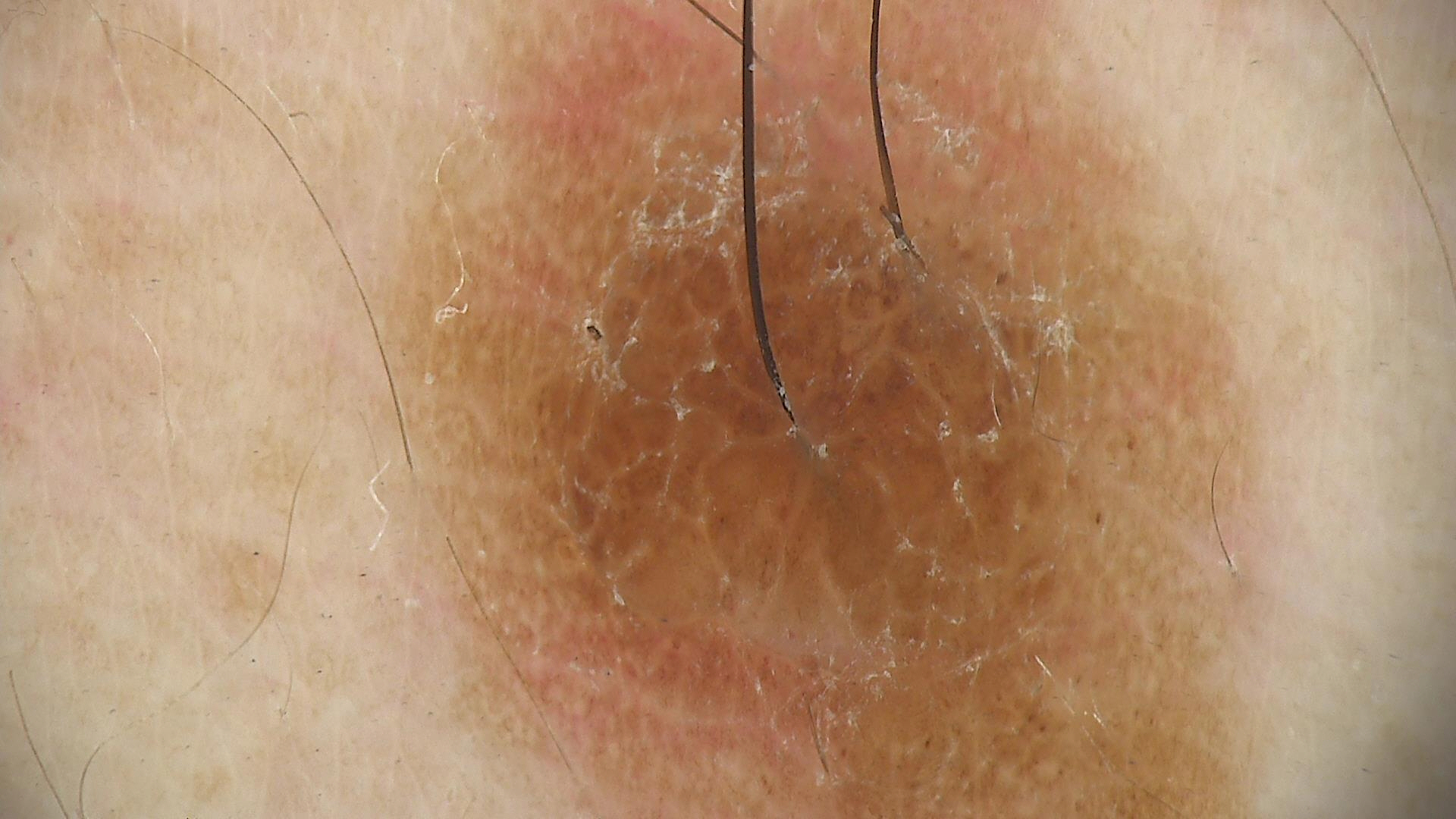The architecture is that of a banal lesion.
Labeled as a compound nevus.